Male patient, age 40–49 · the lesion involves the leg and top or side of the foot · this is a close-up image — 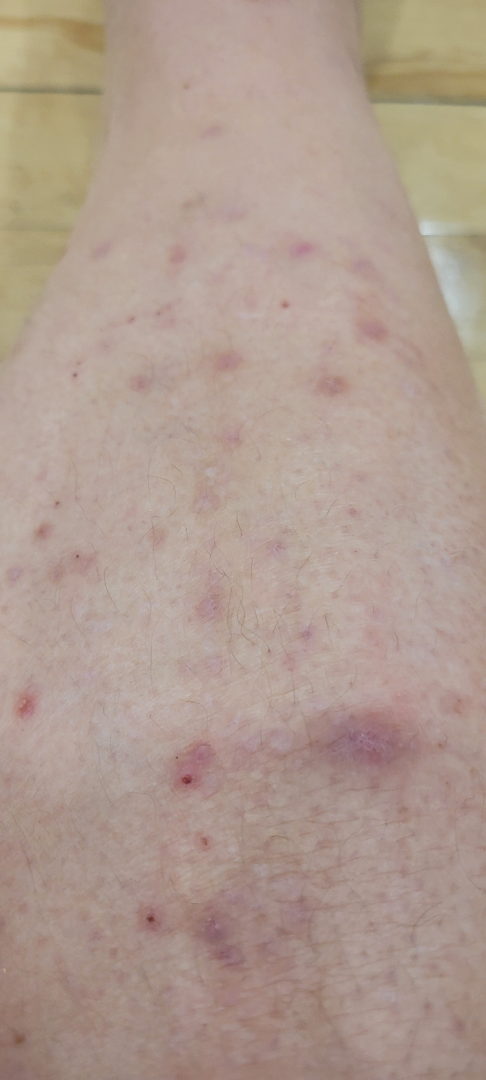texture: raised or bumpy
patient-reported symptoms: bothersome appearance and itching
skin tone: Fitzpatrick I; non-clinician graders estimated 2 on the Monk Skin Tone
patient's own categorization: a rash
duration: one to three months
assessment: the favored diagnosis is Folliculitis; also on the differential is Insect Bite; less probable is Eczema